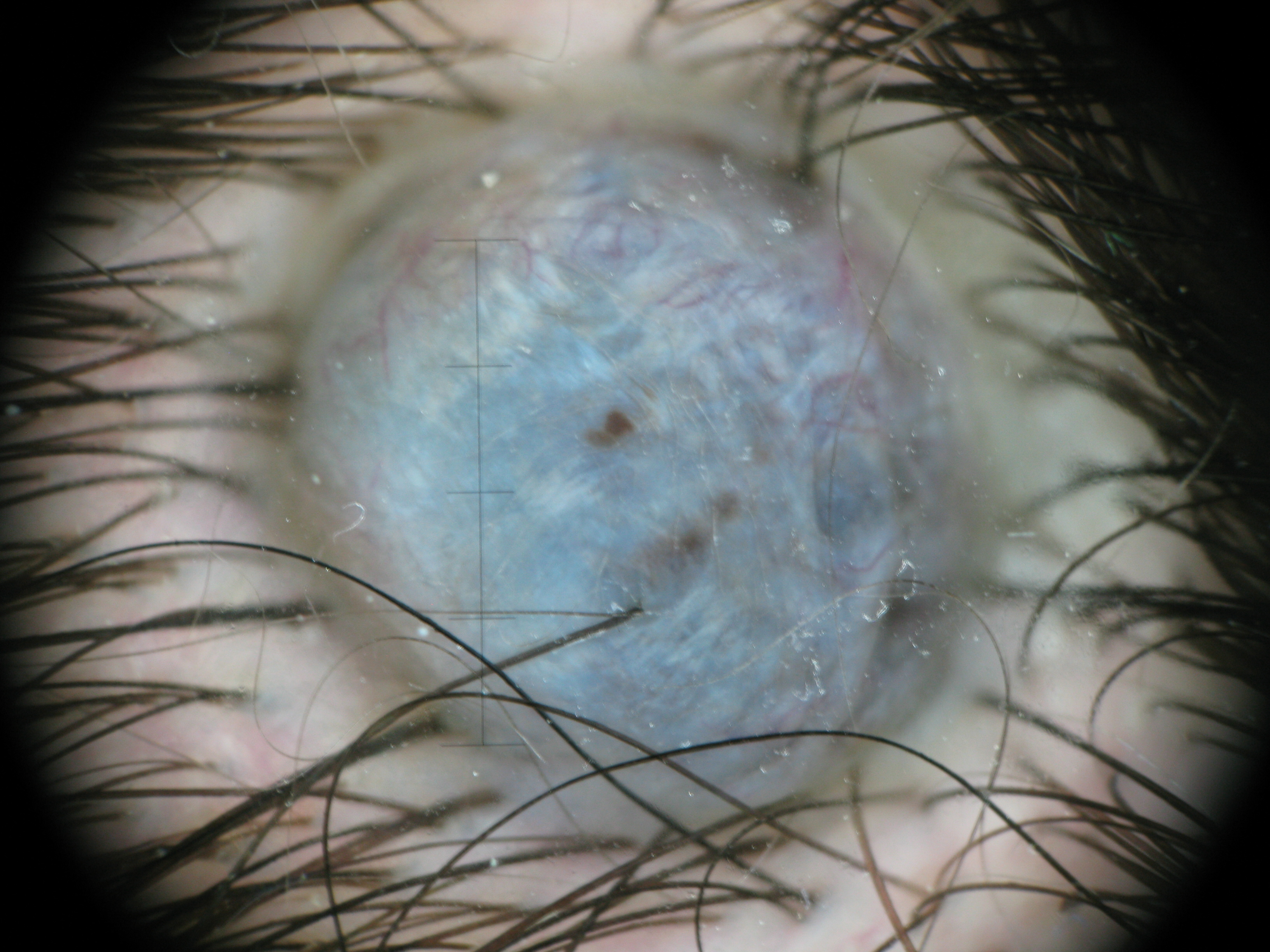A skin lesion imaged with a dermatoscope.
The architecture is that of a dermal, banal lesion.
Labeled as a blue nevus.